A contact-polarized dermoscopy image of a skin lesion. A male subject aged around 60.
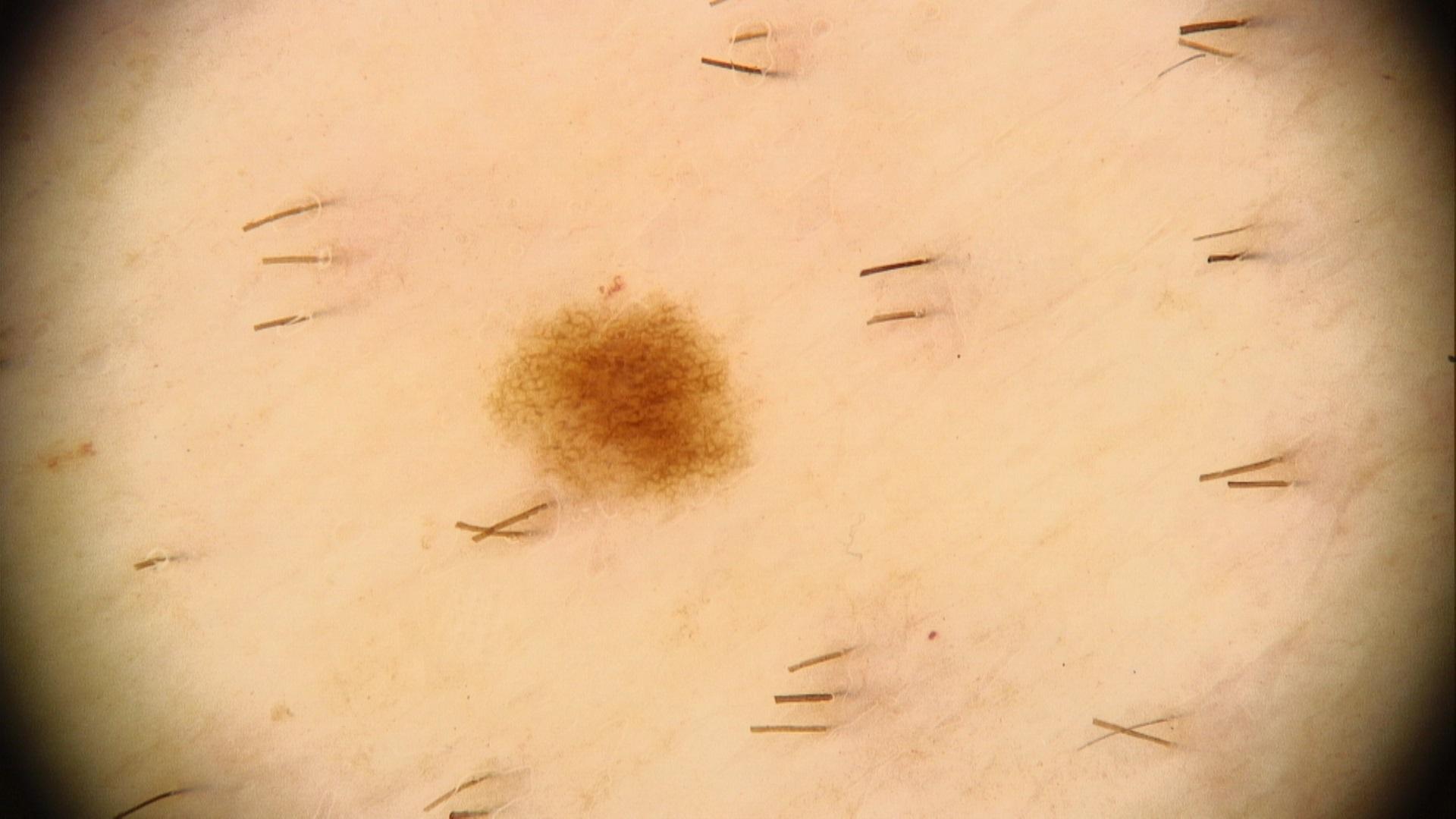• location: the trunk
• diagnosis: Nevus (clinical impression)